A dermoscopic photograph of a skin lesion: 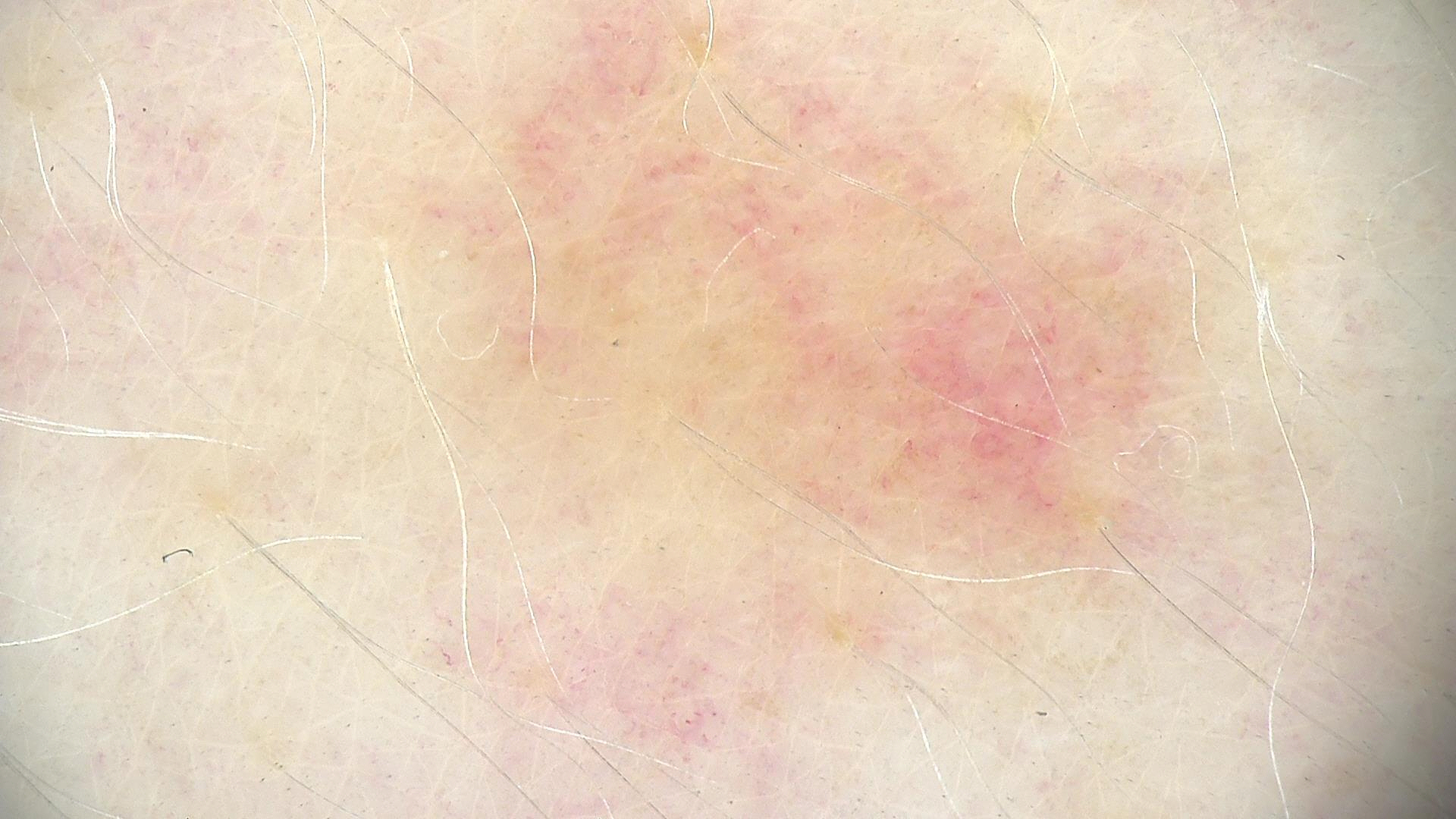label — dermal nevus (expert consensus).